Close-up view — 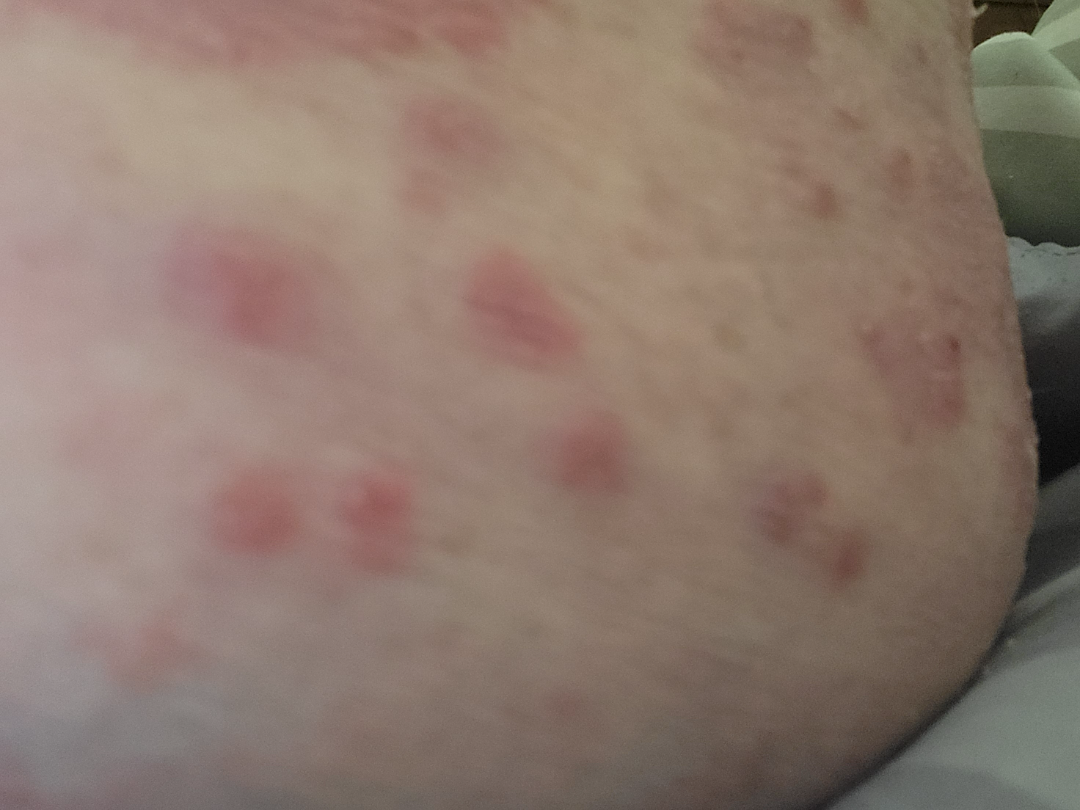No differential diagnosis could be assigned on photographic review.